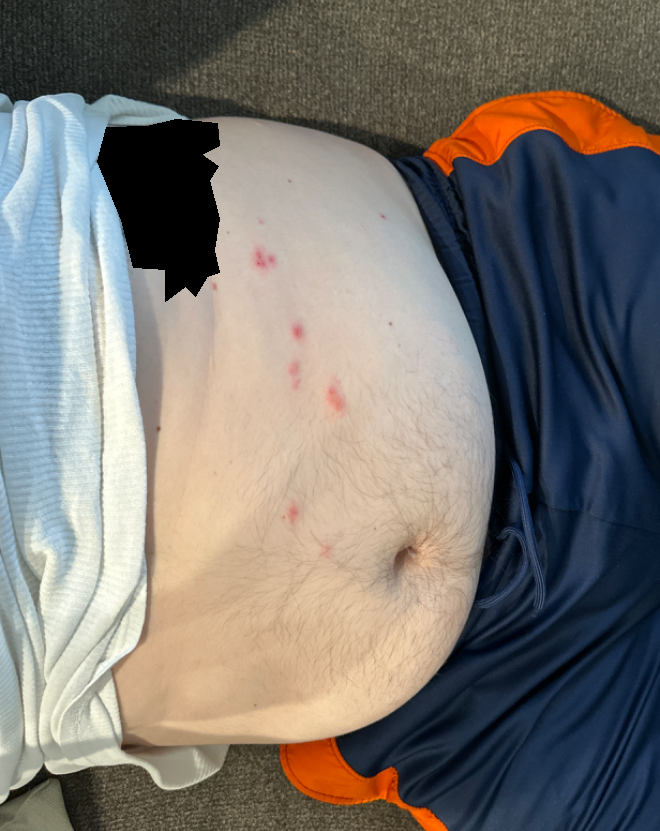assessment: indeterminate from the photograph
image framing: at a distance
subject: male, age 30–39
affected area: front of the torso